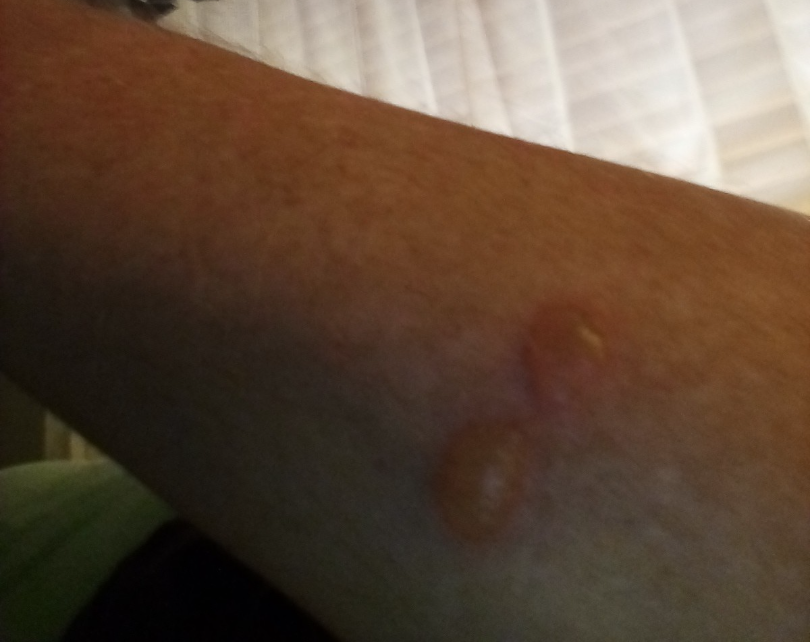<dermatology_case>
  <shot_type>close-up</shot_type>
  <differential>
    <leading>Bullous Pemphigoid</leading>
  </differential>
</dermatology_case>